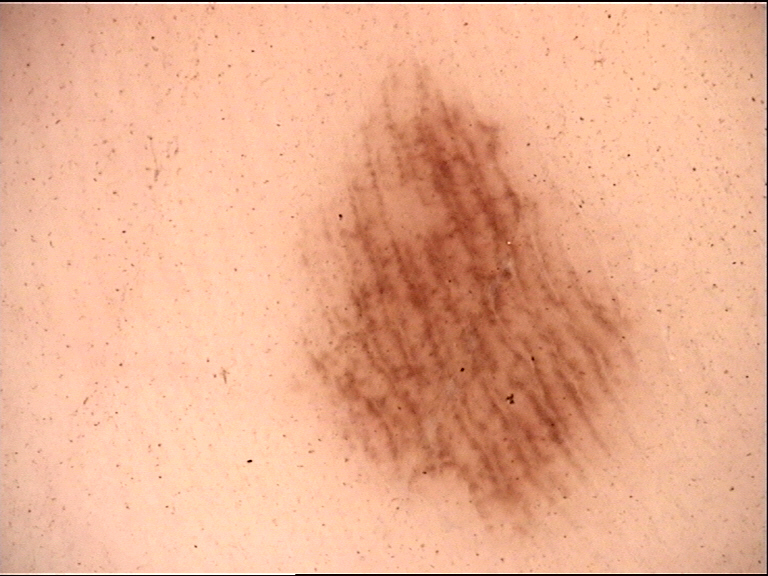A dermoscopic close-up of a skin lesion.
Classified as a banal lesion — an acral junctional nevus.